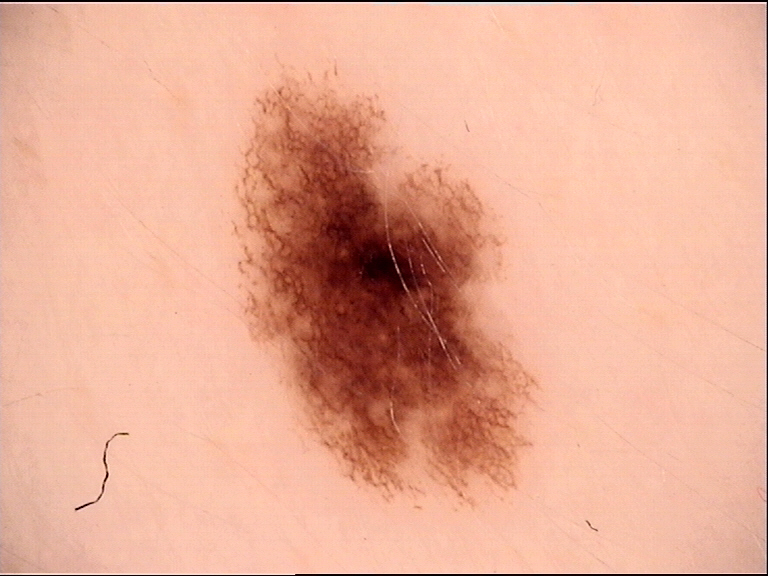- imaging — dermatoscopy
- class — dysplastic junctional nevus (expert consensus)